Dermoscopy of a skin lesion: 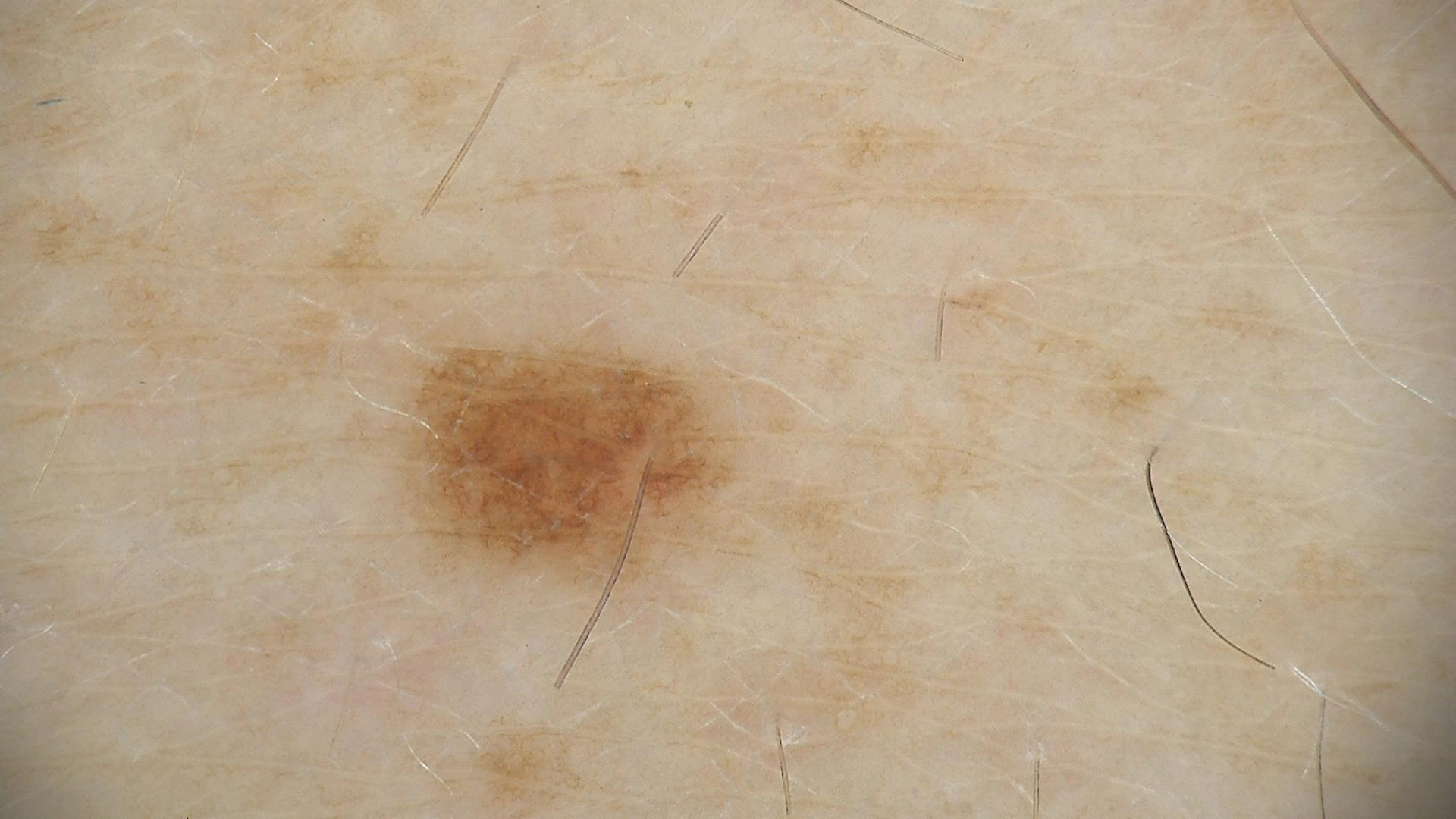{"diagnosis": {"name": "dysplastic junctional nevus", "code": "jd", "malignancy": "benign", "super_class": "melanocytic", "confirmation": "expert consensus"}}